Close-up view, the lesion involves the head or neck: 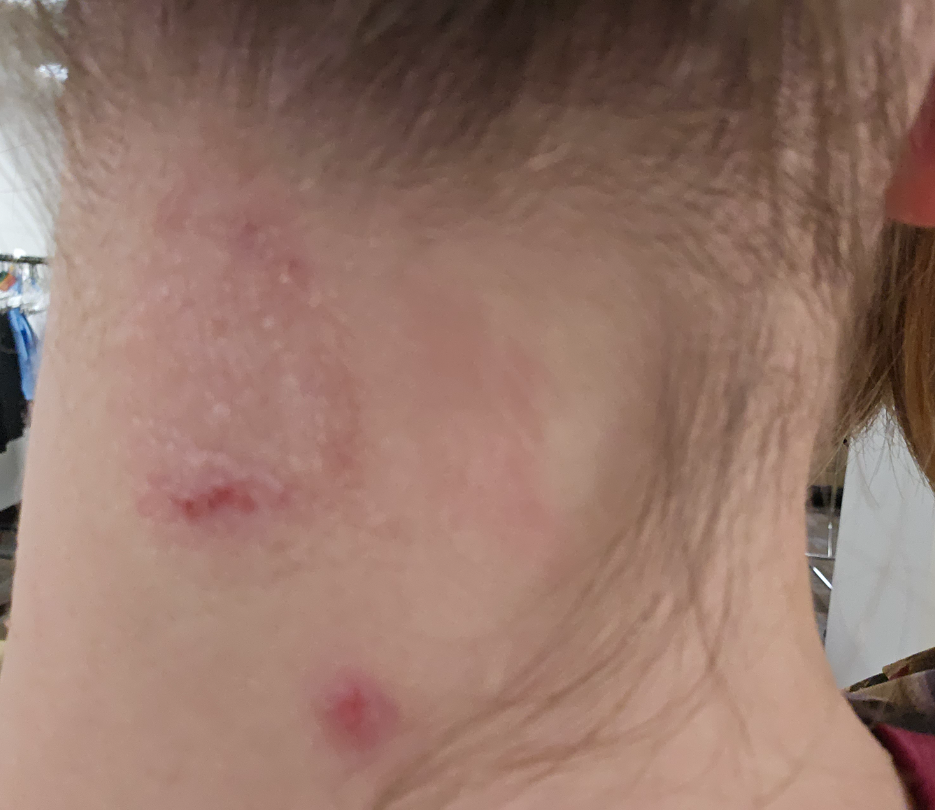Reviewed remotely by one dermatologist: Psoriasis, Eczema and Lichen Simplex Chronicus were each considered, in no particular order.